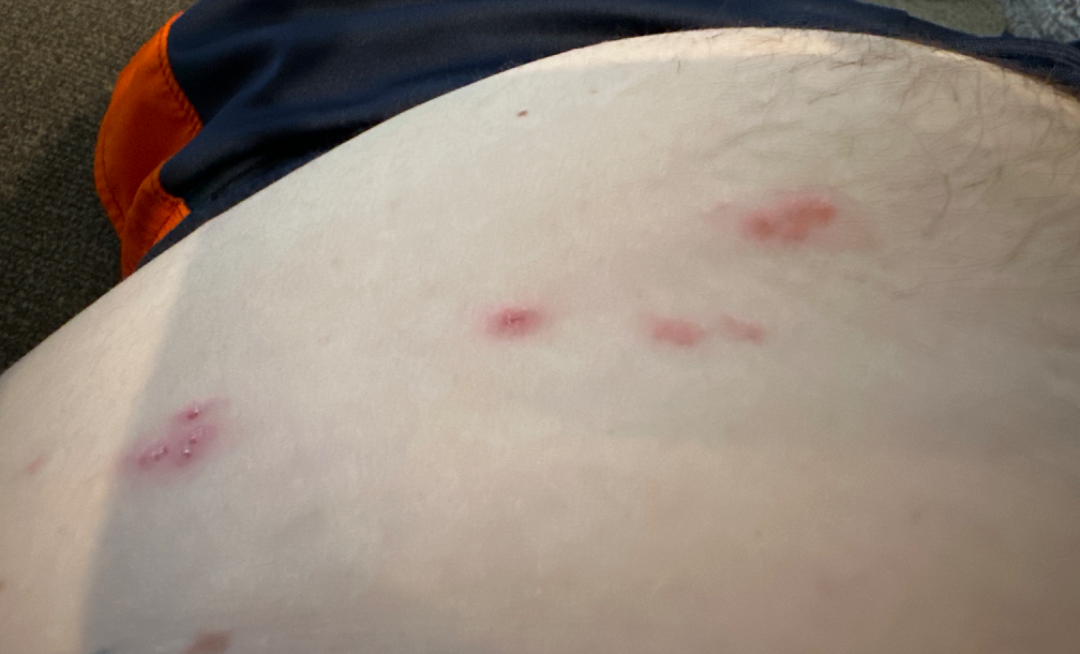The image was not sufficient for the reviewer to characterize the skin condition. Symptoms reported: burning, pain and itching. The photo was captured at an angle. The affected area is the front of the torso. The contributor notes the lesion is raised or bumpy. Self-categorized by the patient as a rash. The contributor notes the condition has been present for less than one week. The subject is 30–39, male.